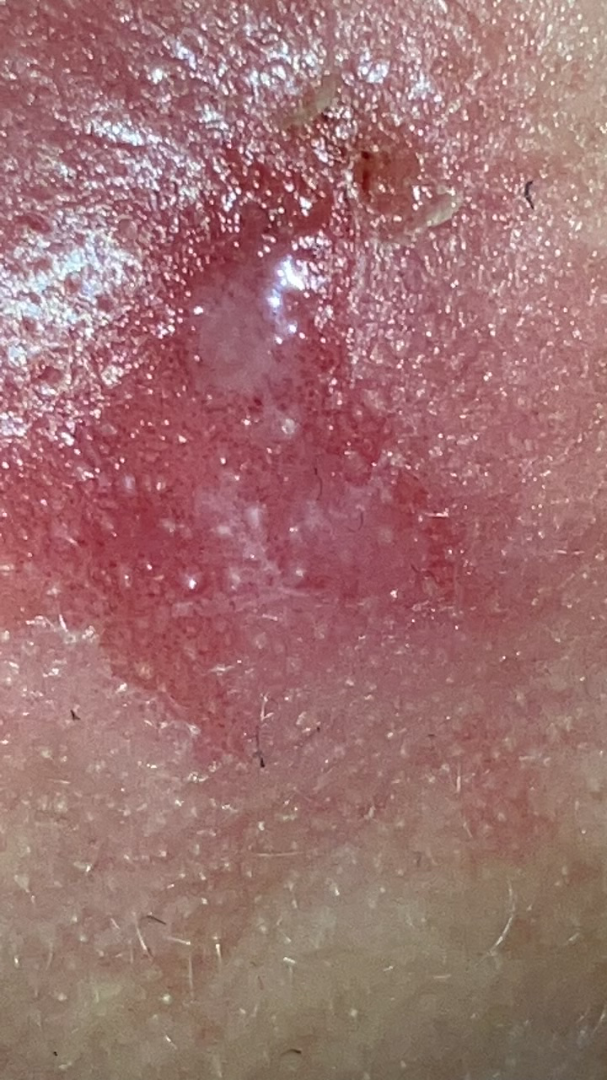Diagnostic features were not clearly distinguishable in this photograph. This is a close-up image. The lesion is associated with pain. The affected area is the head or neck. The patient described the issue as a rash. The patient is female. Texture is reported as fluid-filled. The condition has been present for more than one year.